A male subject about 85 years old or older; a clinical overview photograph of a skin lesion.
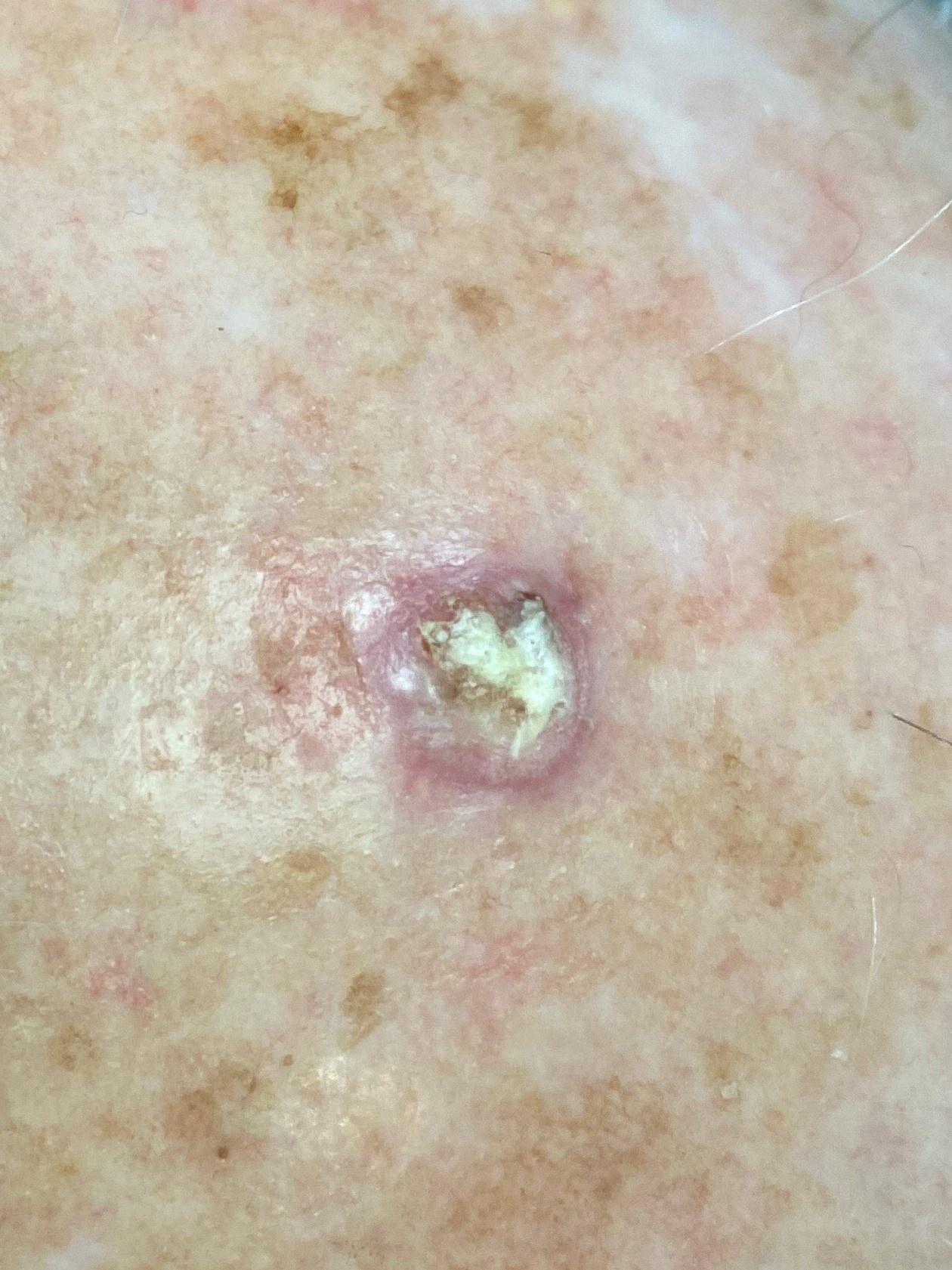Notes:
* body site — the head or neck
* diagnosis — Squamous cell carcinoma (biopsy-proven)